A clinical photograph showing a skin lesion — 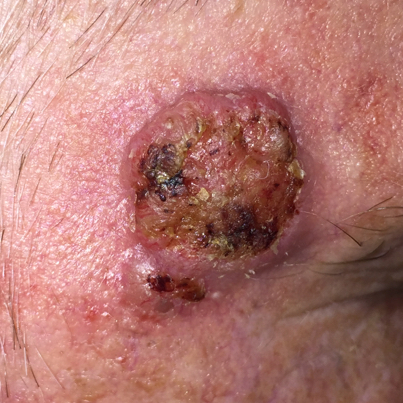<record>
<diagnosis>
<name>basal cell carcinoma</name>
<code>BCC</code>
<malignancy>malignant</malignancy>
<confirmation>histopathology</confirmation>
</diagnosis>
</record>